A dermoscopic photograph of a skin lesion.
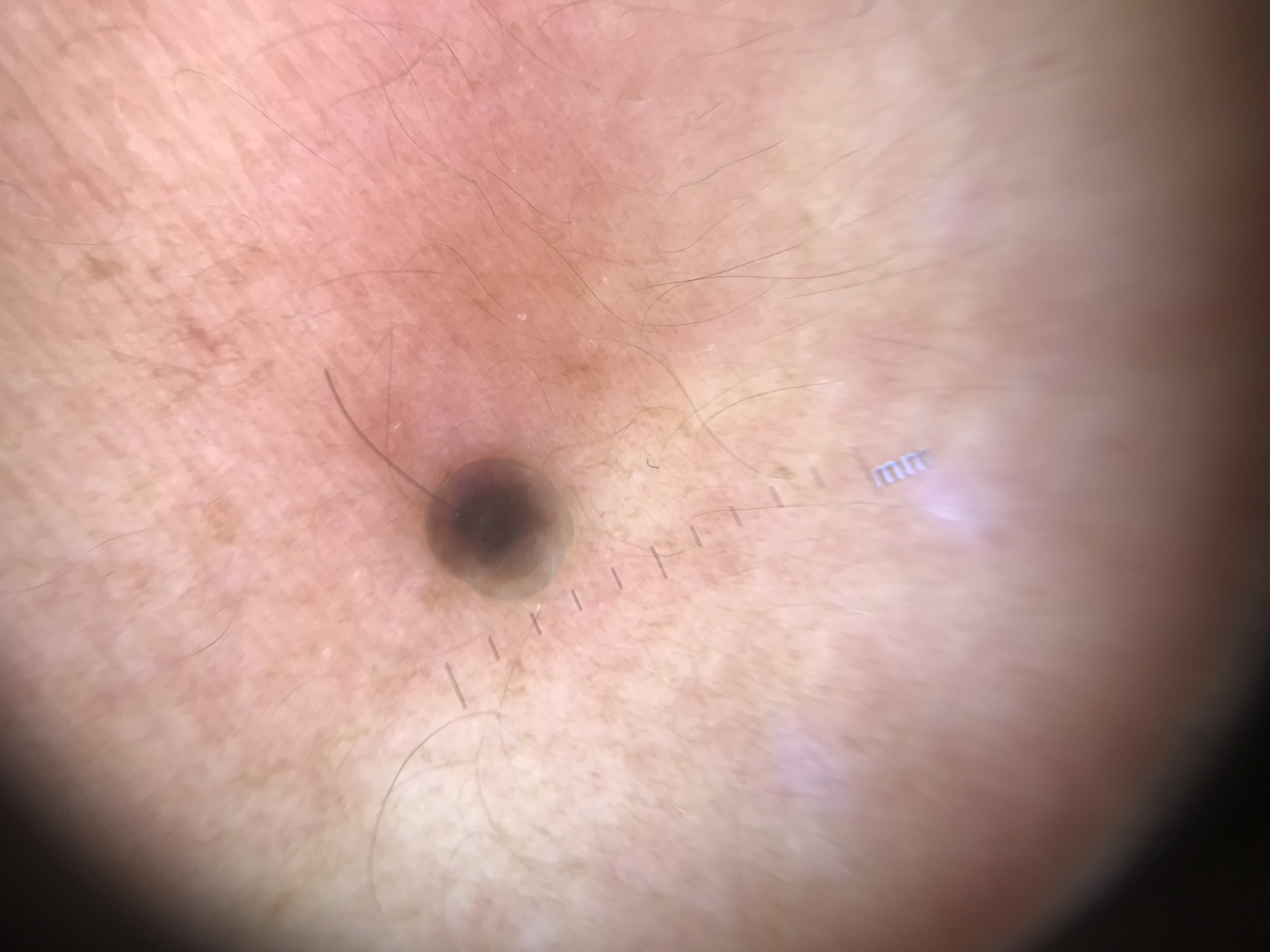Case: The architecture is that of a banal lesion. Conclusion: The diagnosis was a dermal nevus.